No constitutional symptoms were reported. Located on the leg. The lesion is described as flat. The contributor notes burning and itching. The subject is a female aged 18–29. The photo was captured at a distance. Reported duration is about one day. The patient considered this a rash — 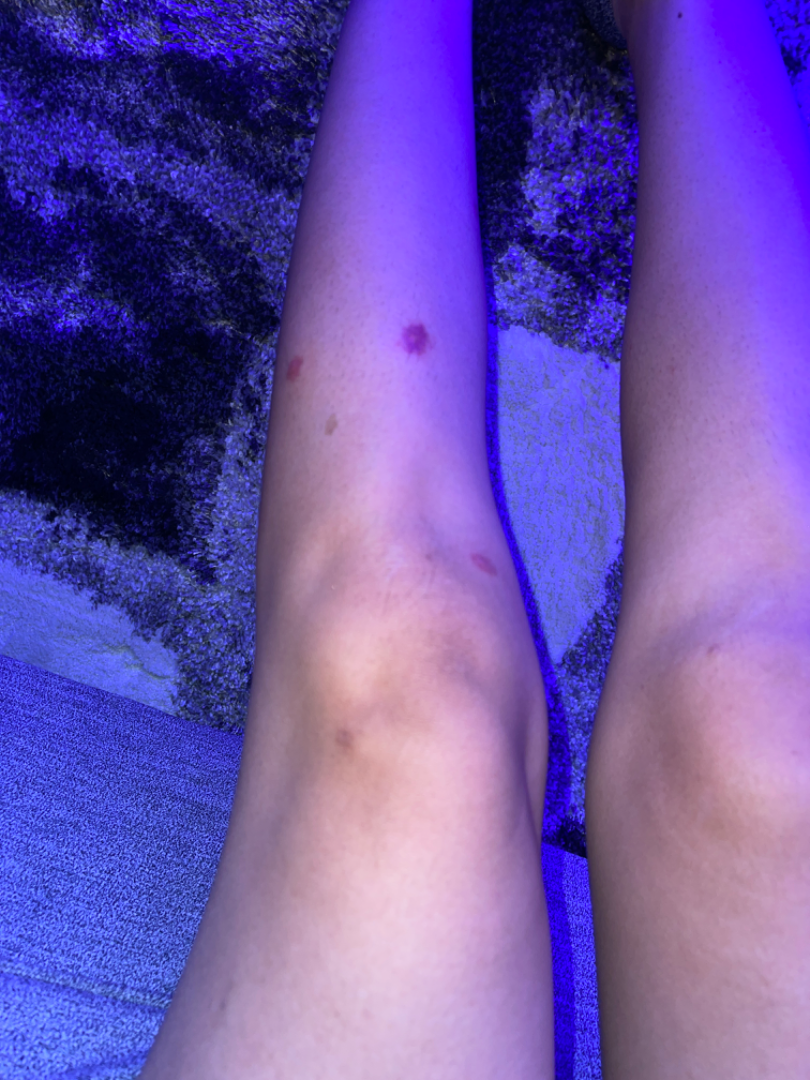assessment = favoring Insect Bite; with consideration of Pigmented purpuric eruption; less probable is Leukemia cutis.